The patient reported no systemic symptoms. This is a close-up image. The leg is involved. Self-categorized by the patient as a rash. The patient reports itching. Reported duration is less than one week — 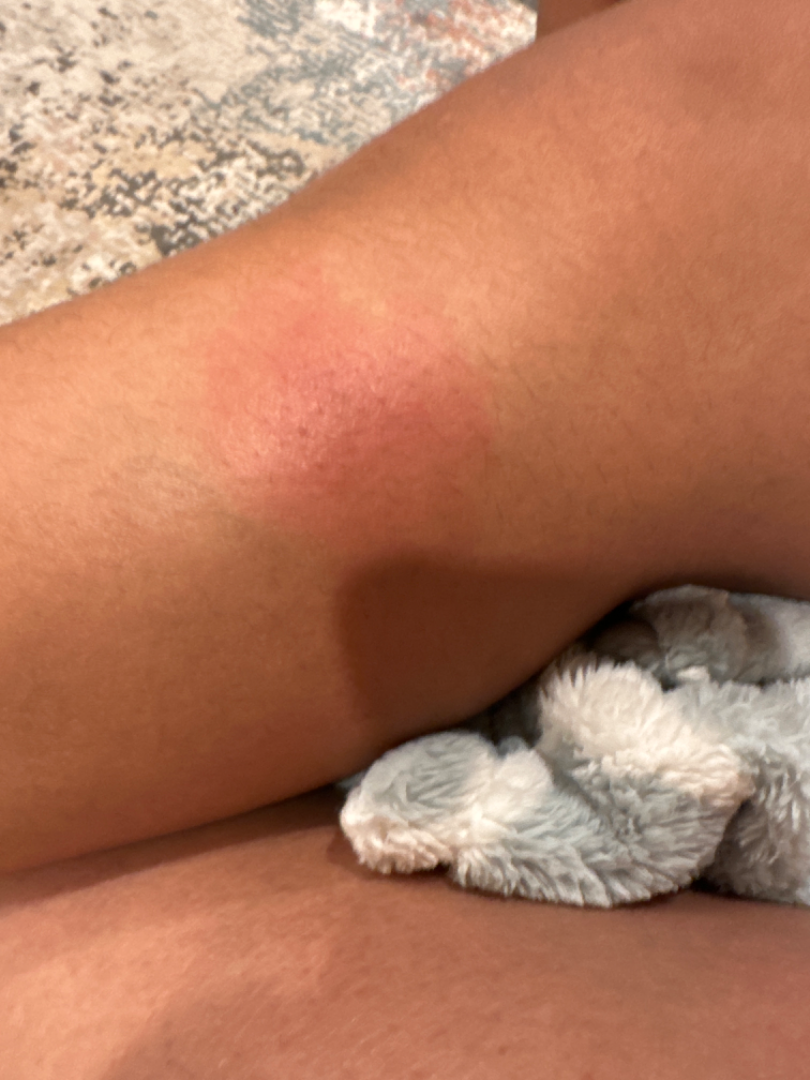Impression: On remote dermatologist review: Cellulitis and Insect Bite were considered with similar weight; a more distant consideration is Acute dermatitis, NOS; less likely is Erythema nodosum; less probable is Drug Rash.